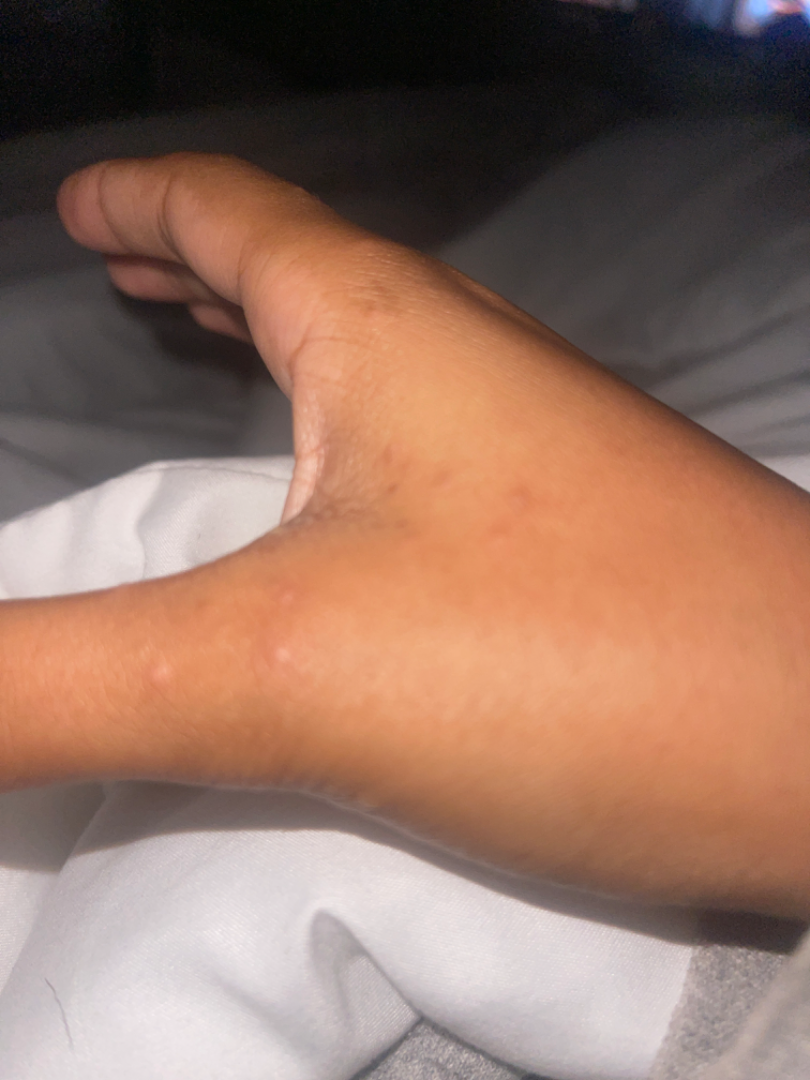Background:
The patient described the issue as a rash. No relevant systemic symptoms. The contributor notes the lesion is fluid-filled and raised or bumpy. Reported lesion symptoms include burning and itching. Female subject, age 18–29. The photograph was taken at an angle. The affected area is the palm, sole of the foot, top or side of the foot and back of the hand.
Findings:
Reviewed remotely by three dermatologists: most consistent with Scabies; also on the differential is Eczema; a remote consideration is Molluscum Contagiosum; less likely is Allergic Contact Dermatitis; less probable is Hypersensitivity.